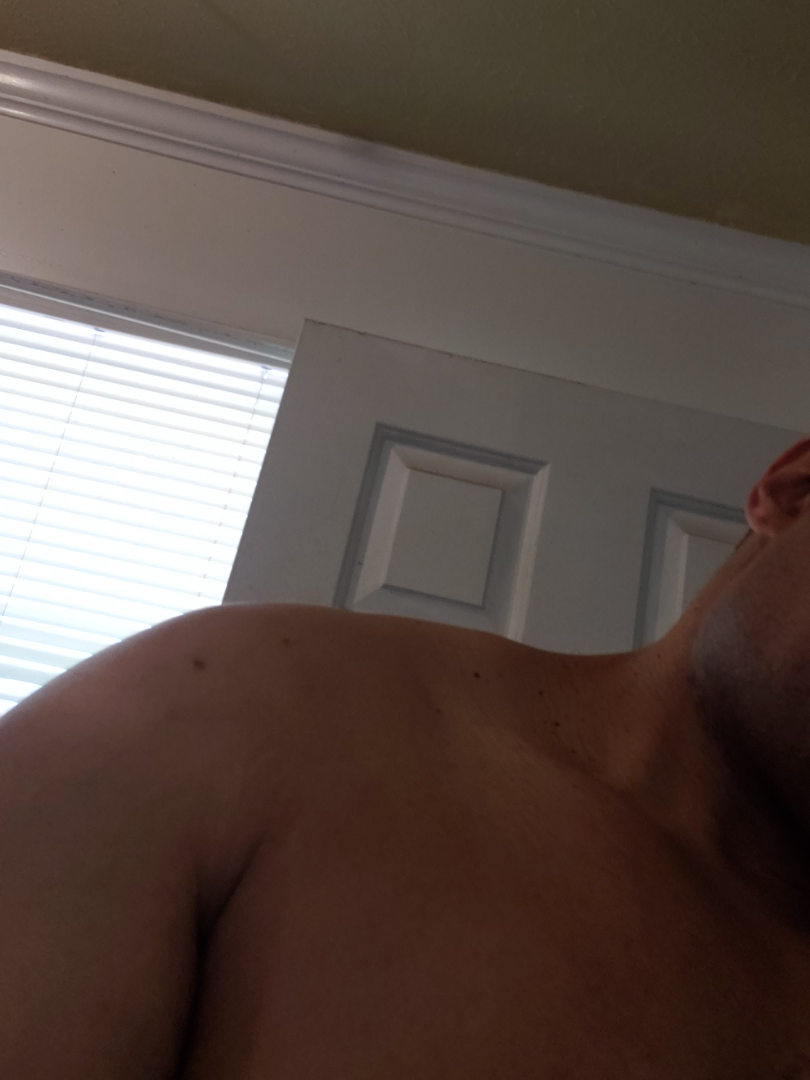No differential diagnosis could be assigned on photographic review. The lesion is described as raised or bumpy. An image taken at a distance. Located on the head or neck. Symptoms reported: bothersome appearance. Self-categorized by the patient as a growth or mole. The condition has been present for more than five years. Male contributor, age 40–49.